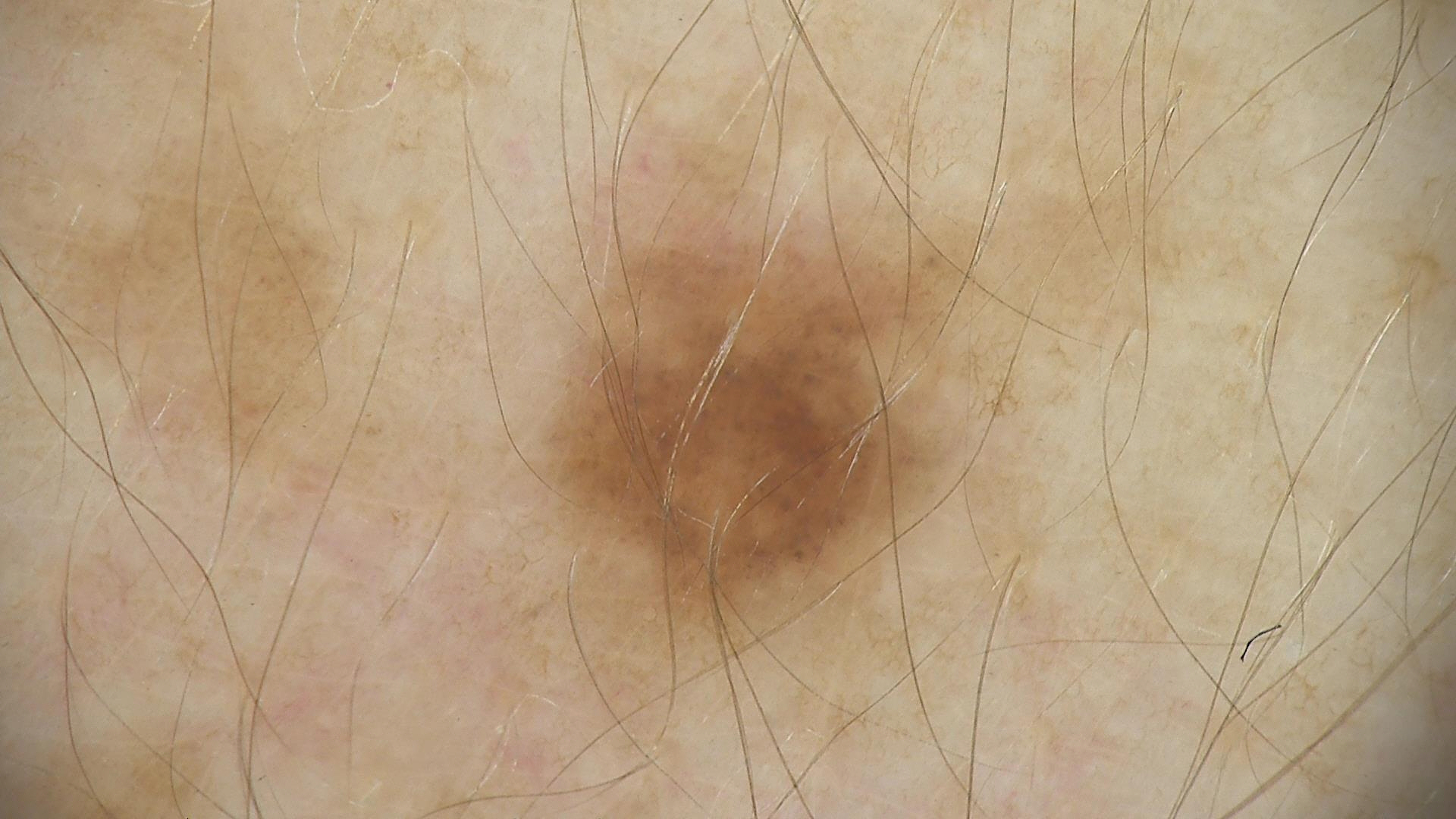image: dermatoscopy
diagnosis:
  name: dysplastic junctional nevus
  code: jd
  malignancy: benign
  super_class: melanocytic
  confirmation: expert consensus